A female patient roughly 50 years of age — 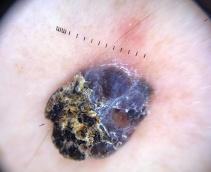Located on a lower extremity. Histopathological examination showed a melanoma.